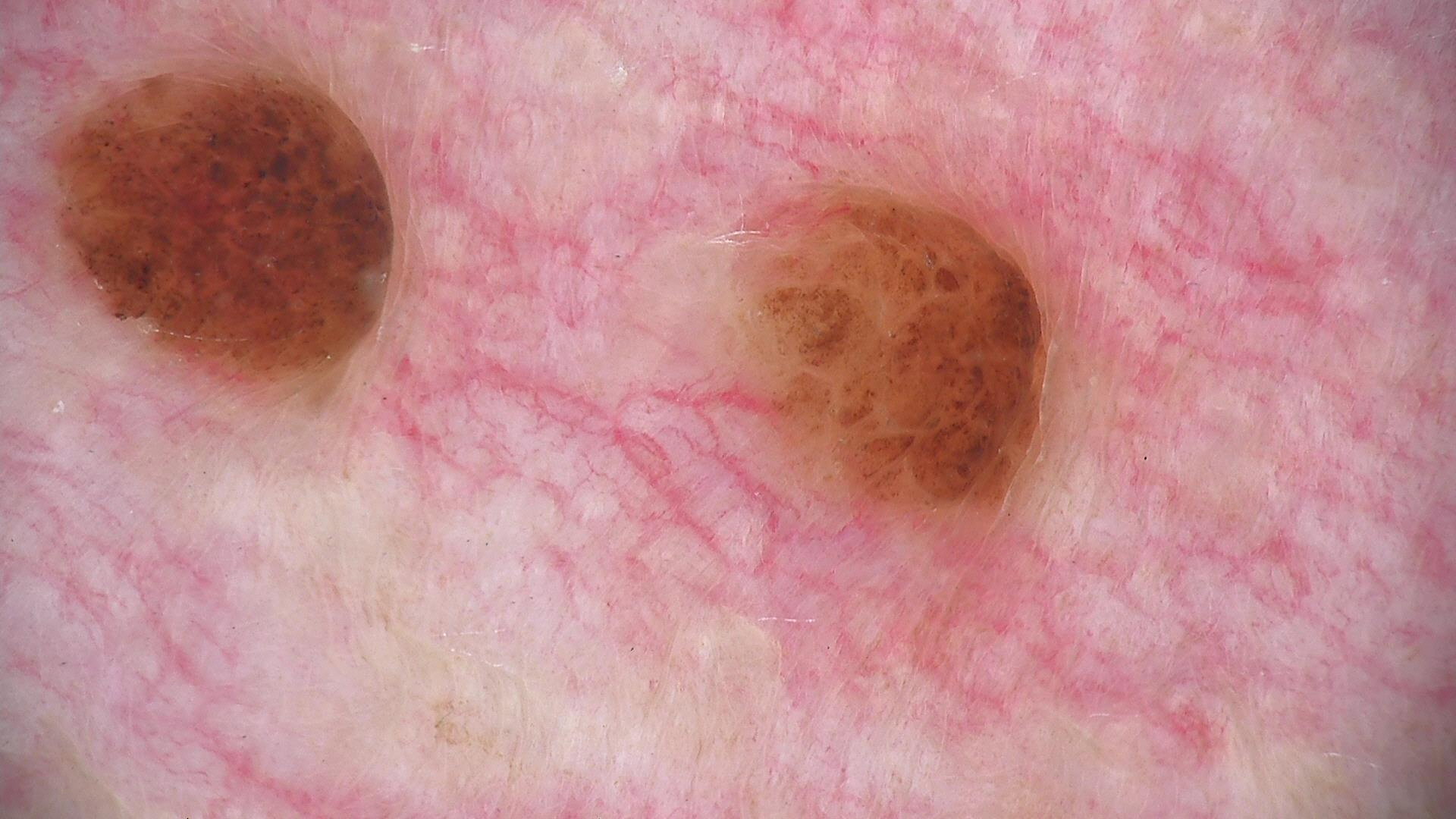diagnosis: dermal nevus (expert consensus)